A dermoscopic image of a skin lesion: 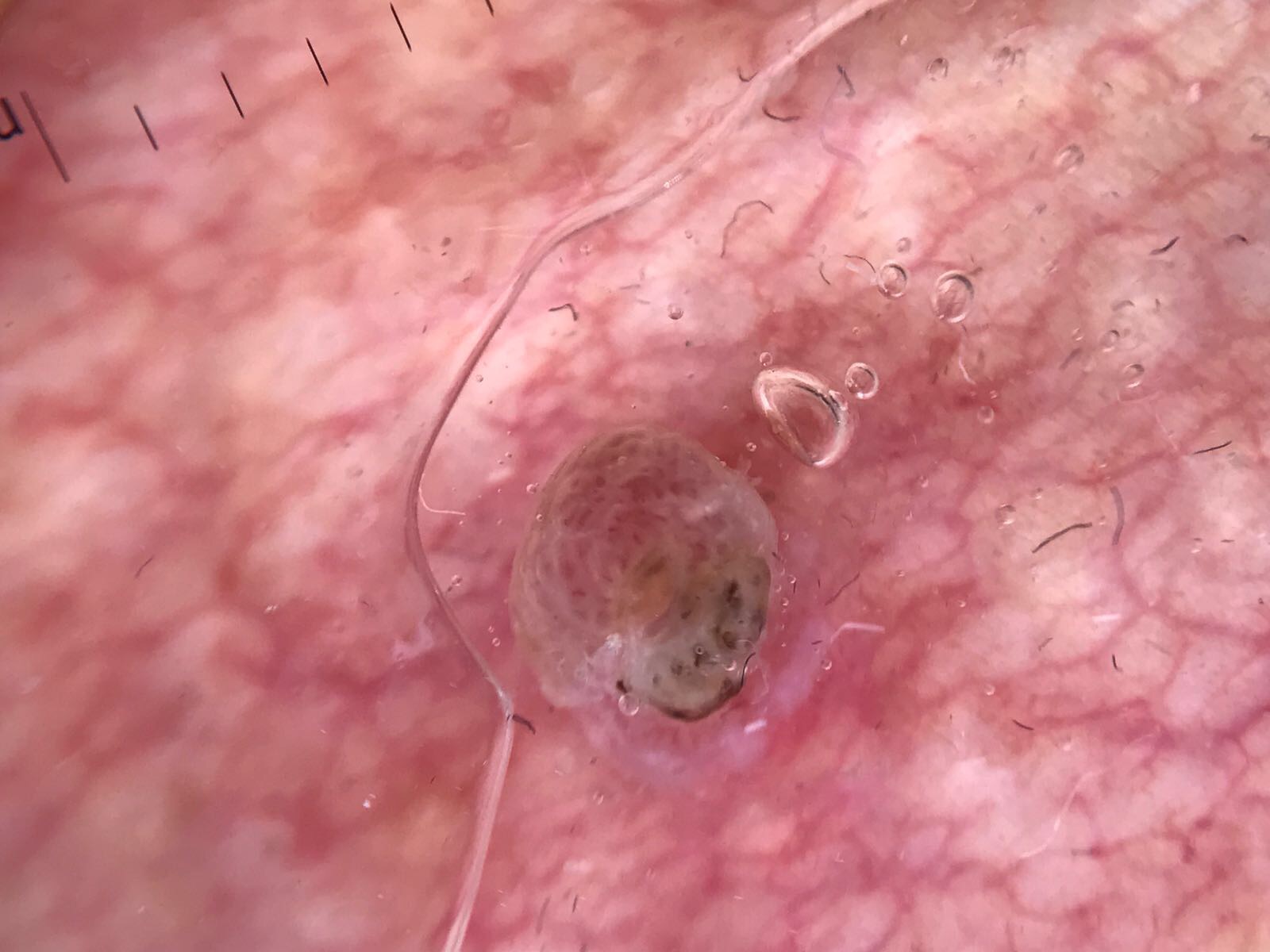Confirmed on histopathology as a malignant, keratinocytic lesion — a squamous cell carcinoma.